A skin lesion imaged with a dermatoscope:
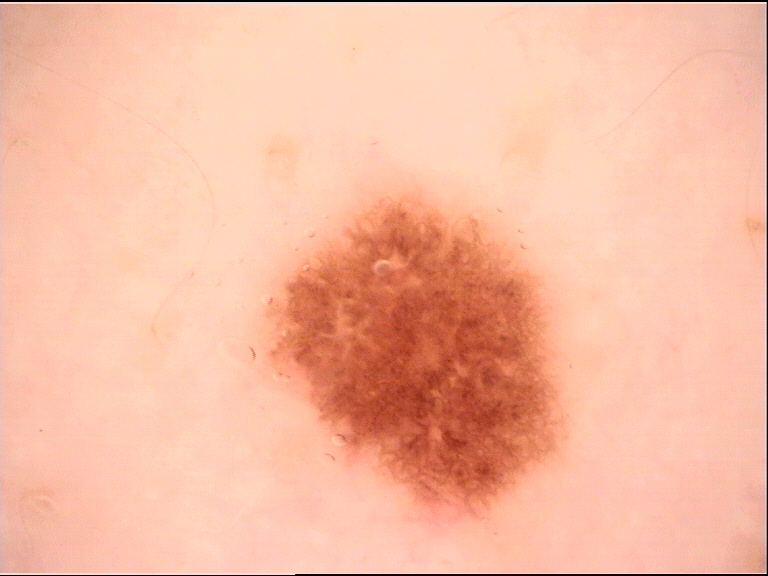diagnosis = dysplastic junctional nevus (expert consensus).